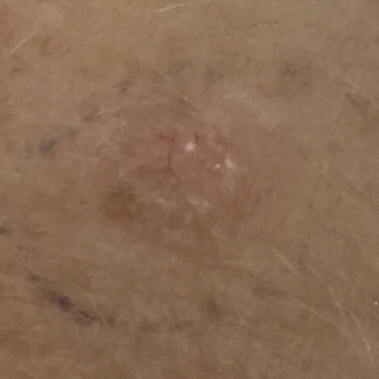Q: Tell me about the patient.
A: female, 52 years of age
Q: What kind of image is this?
A: clinical photo
Q: Skin phototype?
A: II
Q: What is the anatomic site?
A: the face
Q: What are the lesion's dimensions?
A: 6 × 5 mm
Q: What symptoms does the patient report?
A: growth, elevation, bleeding, itching
Q: What is this lesion?
A: basal cell carcinoma (biopsy-proven)